A subject in their 70s · a smartphone photograph of a skin lesion:
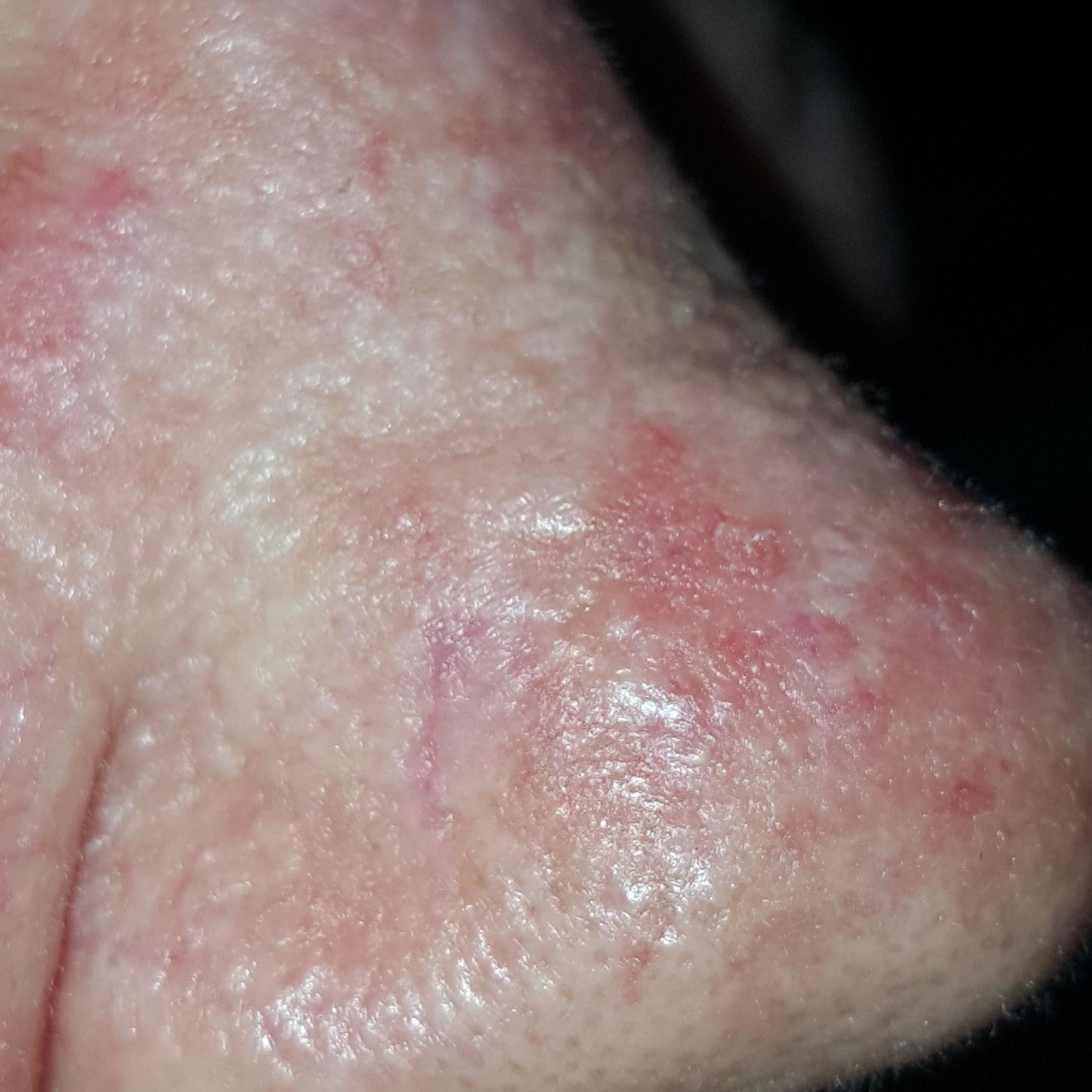Findings:
The lesion is located on the nose. The patient describes that the lesion has grown and itches.
Conclusion:
Clinically diagnosed as an actinic keratosis.